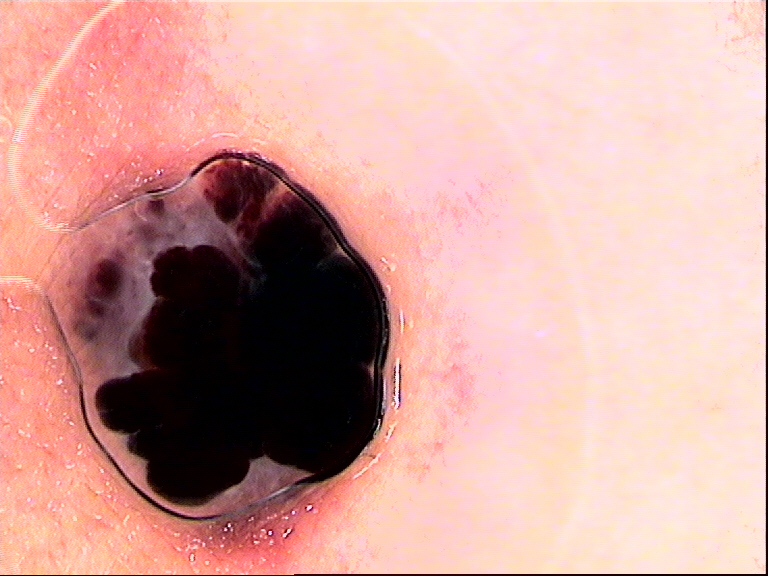Conclusion:
The diagnostic label was an angiokeratoma.